A female patient aged 54. Collected as part of a research study, without a referral diagnosis: 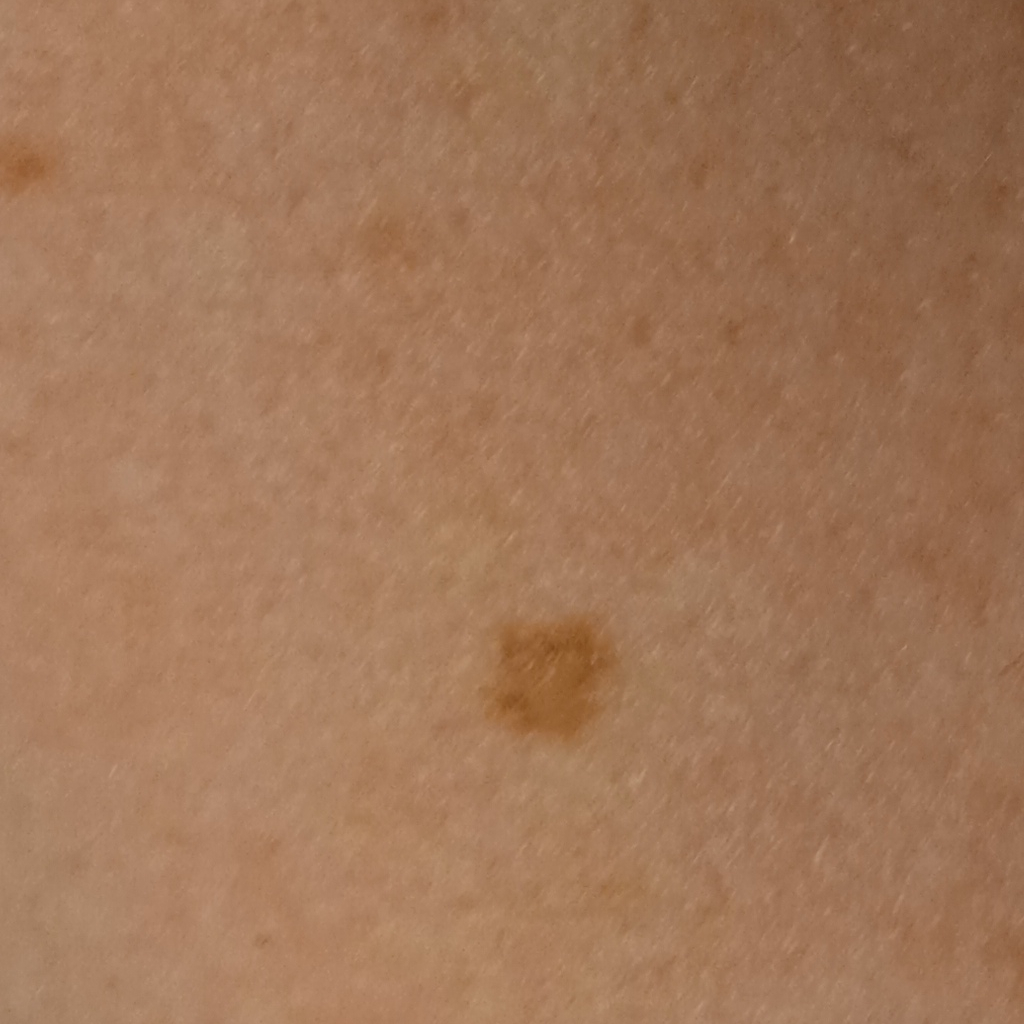| feature | finding |
|---|---|
| site | an arm |
| lesion size | 4.7 mm |
| diagnostic label | atypical (dysplastic) nevus — dermatologist consensus |